Female patient, age 50–59 · the affected area is the front of the torso · an image taken at a distance.
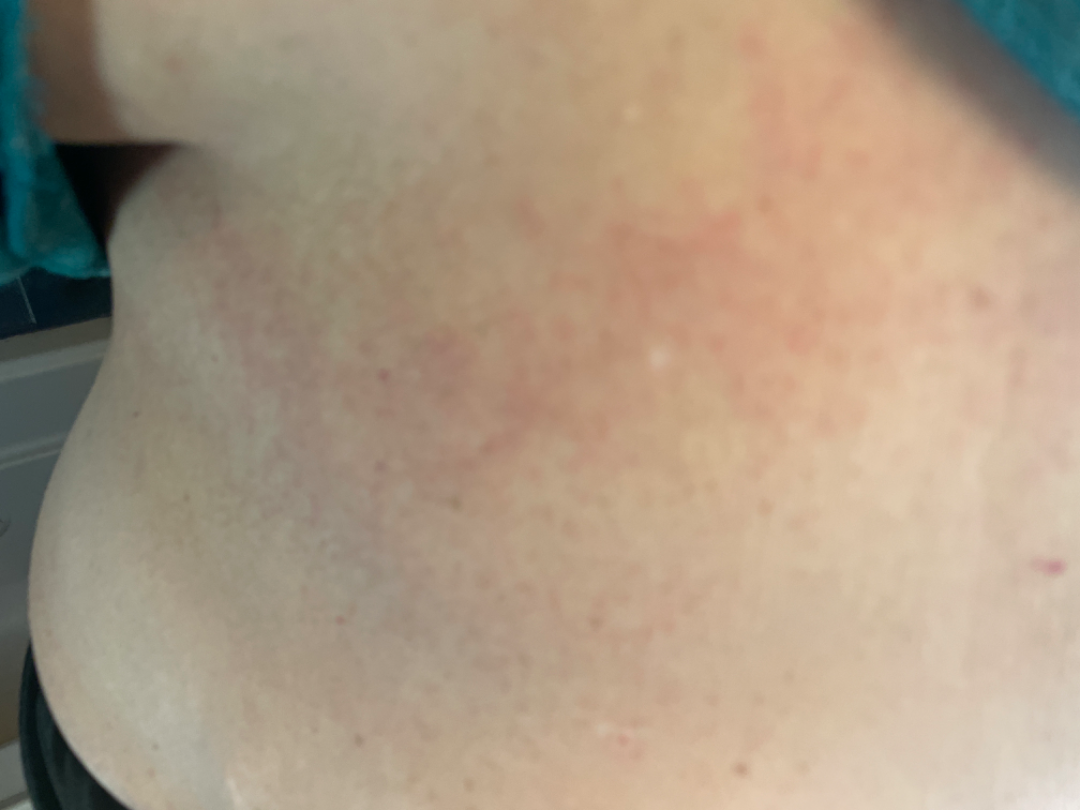Case summary:
• described texture: raised or bumpy
• associated systemic symptoms: fatigue and chills
• lesion symptoms: itching and burning
• onset: less than one week
• assessment: Allergic Contact Dermatitis (44%); Hypersensitivity (26%); Drug Rash (17%); Eczema (14%)